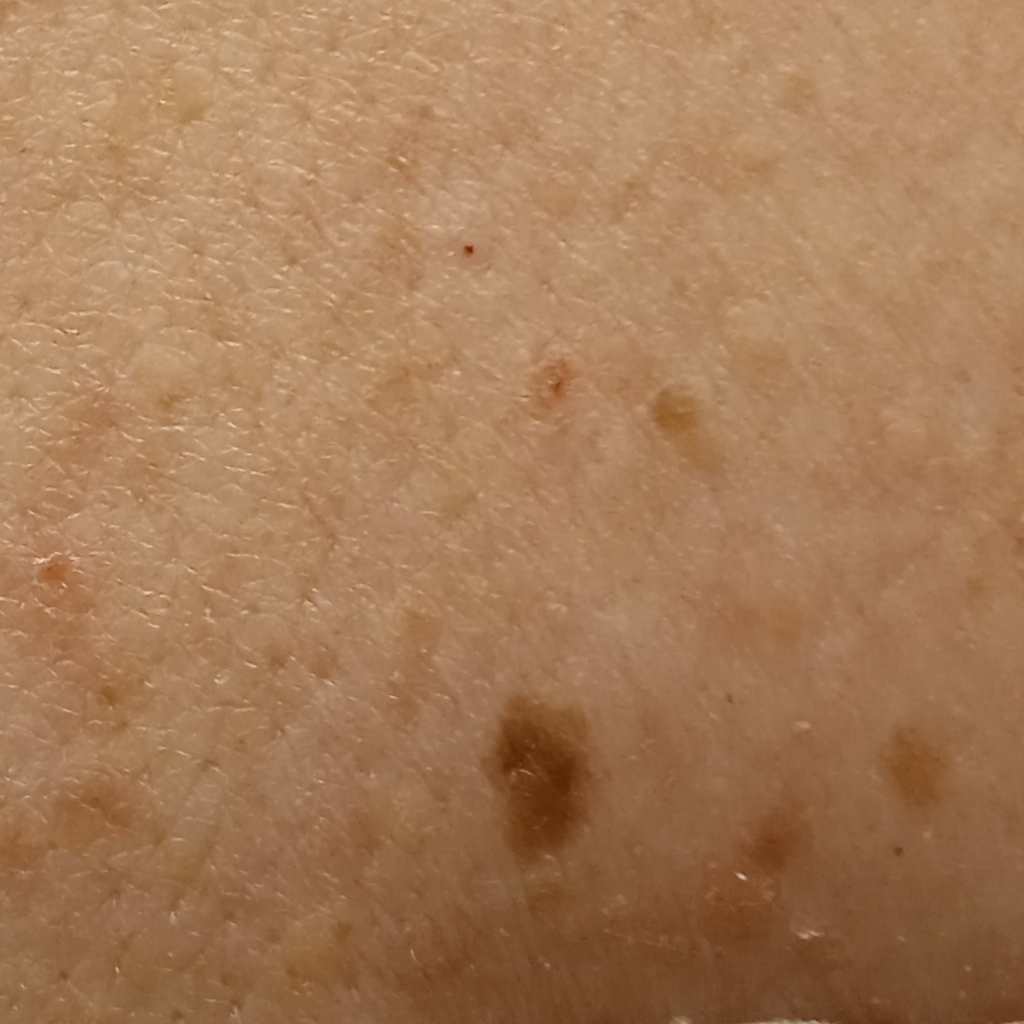Q: What kind of image is this?
A: clinical photo
Q: Patient demographics?
A: female, 55 years old
Q: What is the referral context?
A: research study (no referral diagnosis)
Q: Where is the lesion?
A: the back
Q: How large is the lesion?
A: 6.3 mm
Q: What was the diagnosis?
A: melanocytic nevus (dermatologist consensus)